Skin tone: FST III · the subject is 40–49, female · the lesion involves the head or neck and arm · texture is reported as raised or bumpy and fluid-filled · the patient described the issue as a rash · the photograph was taken at an angle · present for one to four weeks.
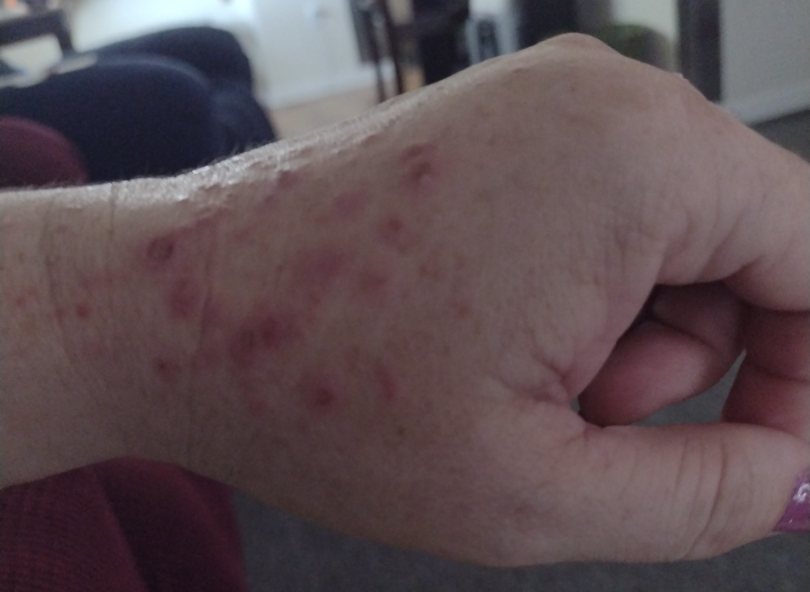<case>
  <assessment>not assessable</assessment>
</case>